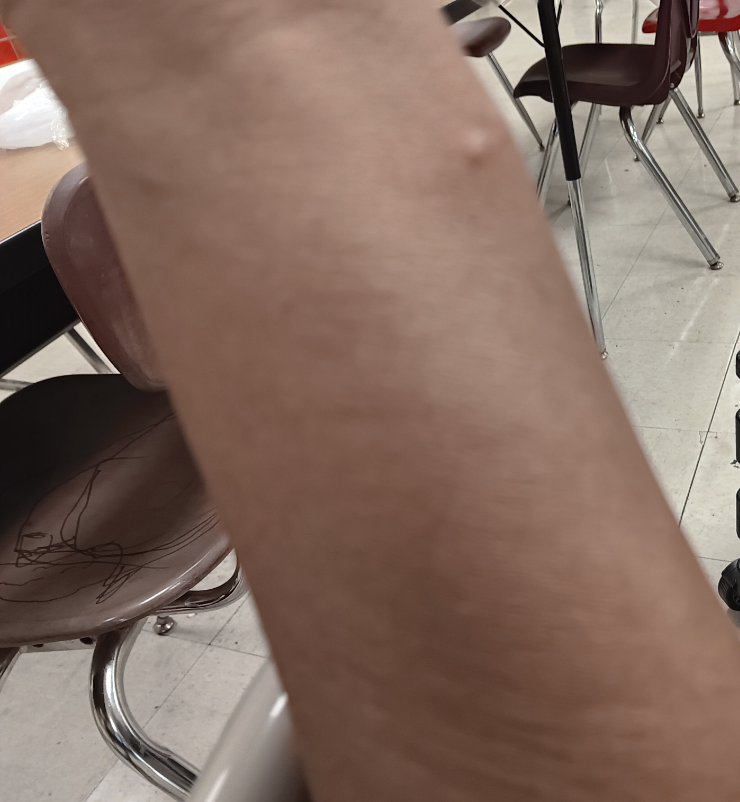The photograph was taken at an angle.
Cyst (weight 0.67); Calcinosis cutis (weight 0.33).